A dermoscopic image of a skin lesion.
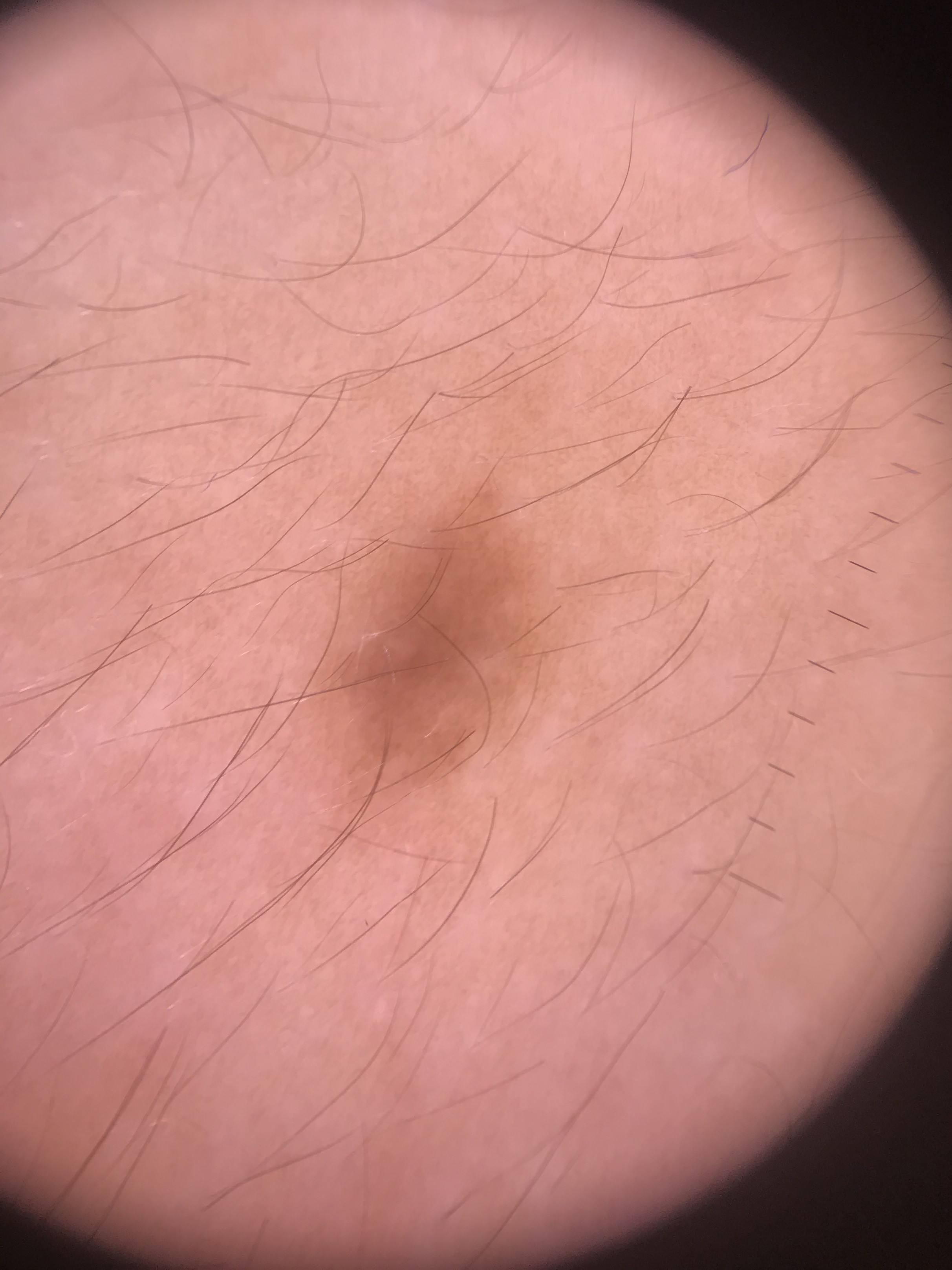The architecture is that of a banal lesion.
The diagnostic label was a junctional nevus.